The condition has been present for one to four weeks · the affected area is the back of the torso, leg, front of the torso and arm · skin tone: Fitzpatrick phototype II · this image was taken at an angle.
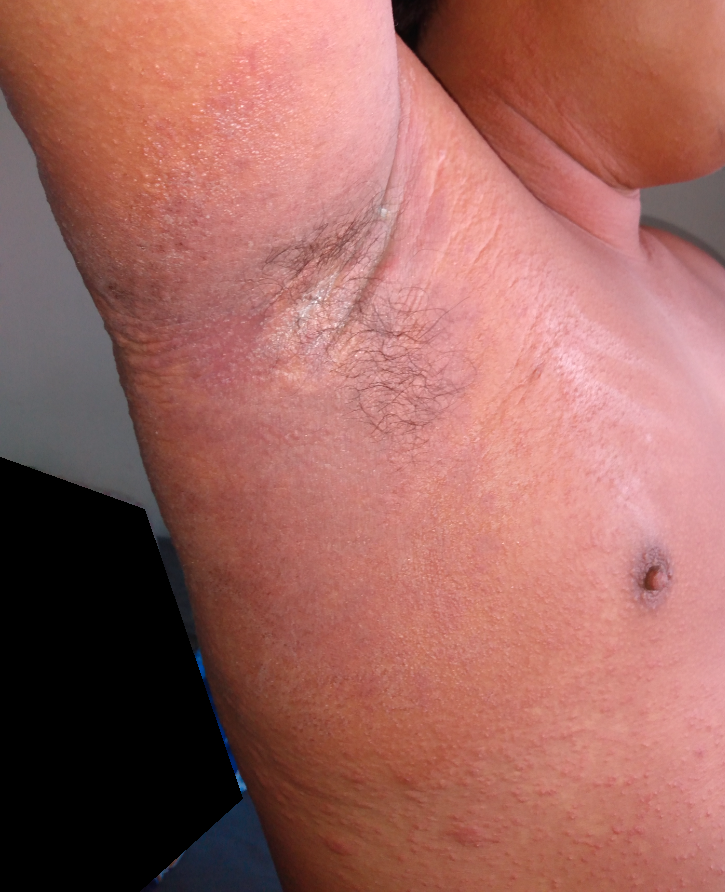Notes:
- dermatologist impression · one reviewing dermatologist: most likely Viral Exanthem; with consideration of Drug Rash; less likely is Hypersensitivity